A female patient in their mid-20s:
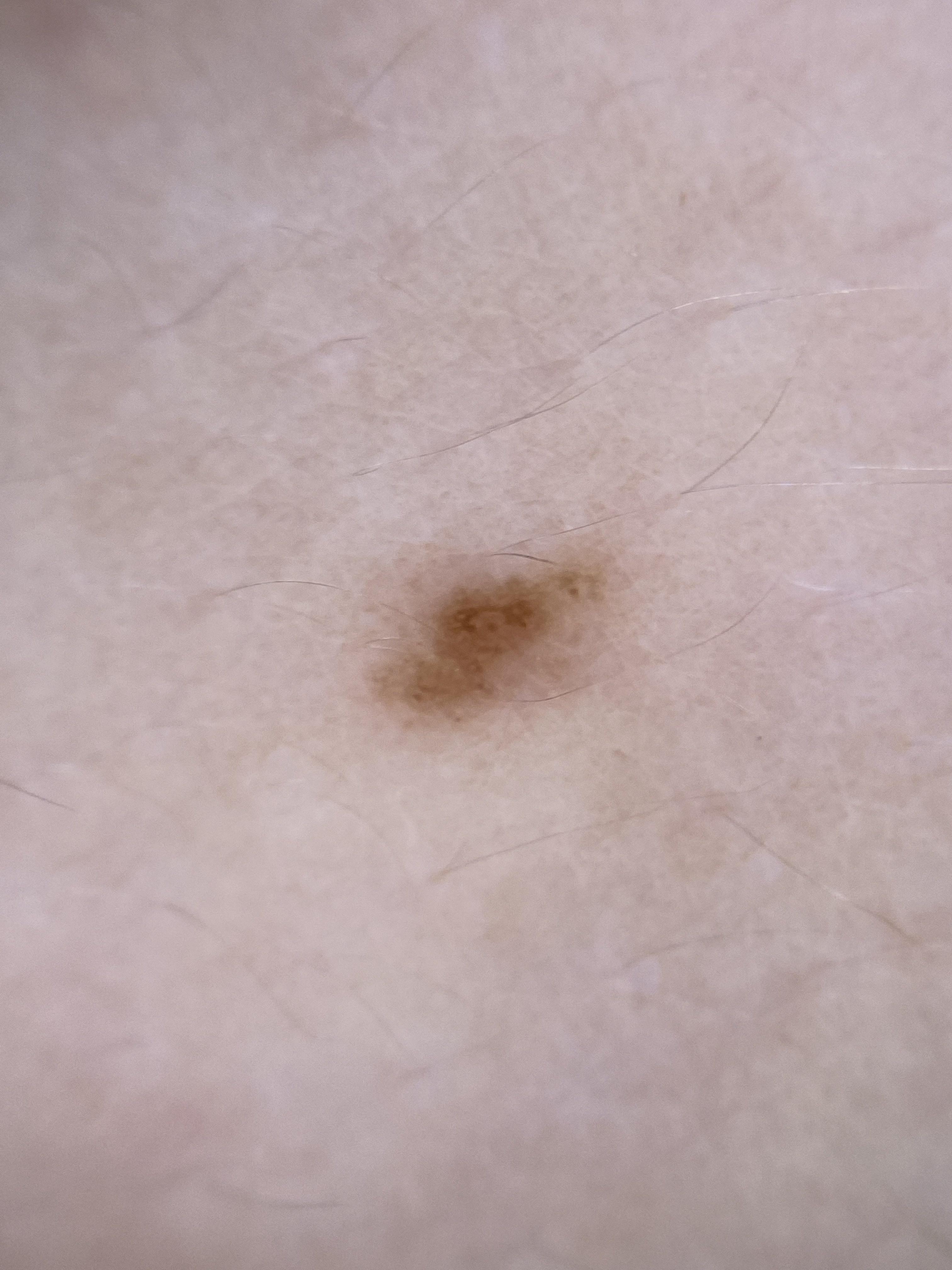diagnosis = Nevus (clinical impression).